A dermoscopic photograph of a skin lesion.
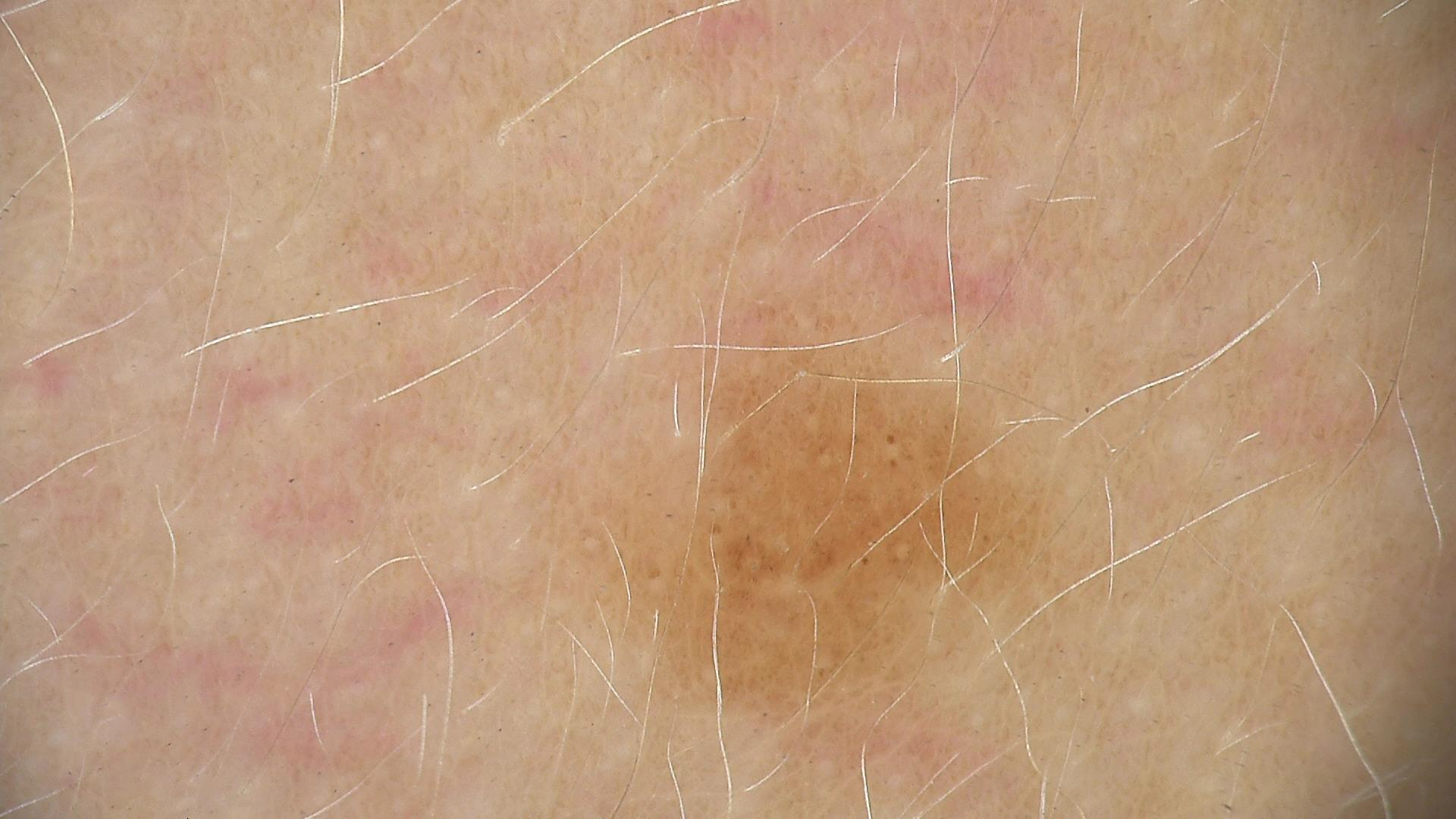Classified as a benign lesion — a dysplastic junctional nevus.